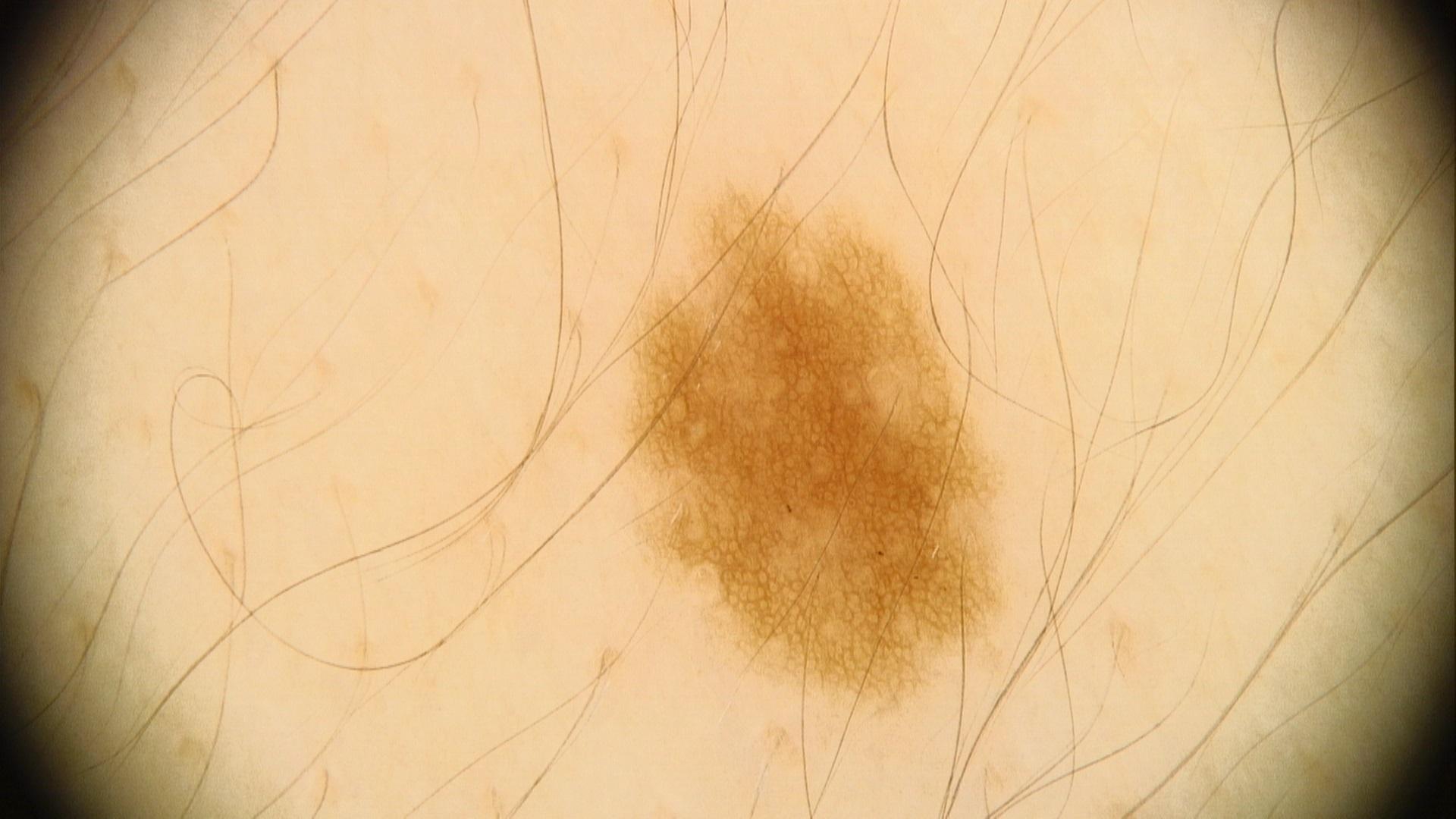Per the chart, melanoma in a first-degree relative but no prior melanoma. Dermoscopy of a skin lesion. A female subject aged 18-22. Expert review favored a lesion of melanocytic origin — a nevus.